Located on the arm and leg · the contributor is 40–49, female · this is a close-up image:
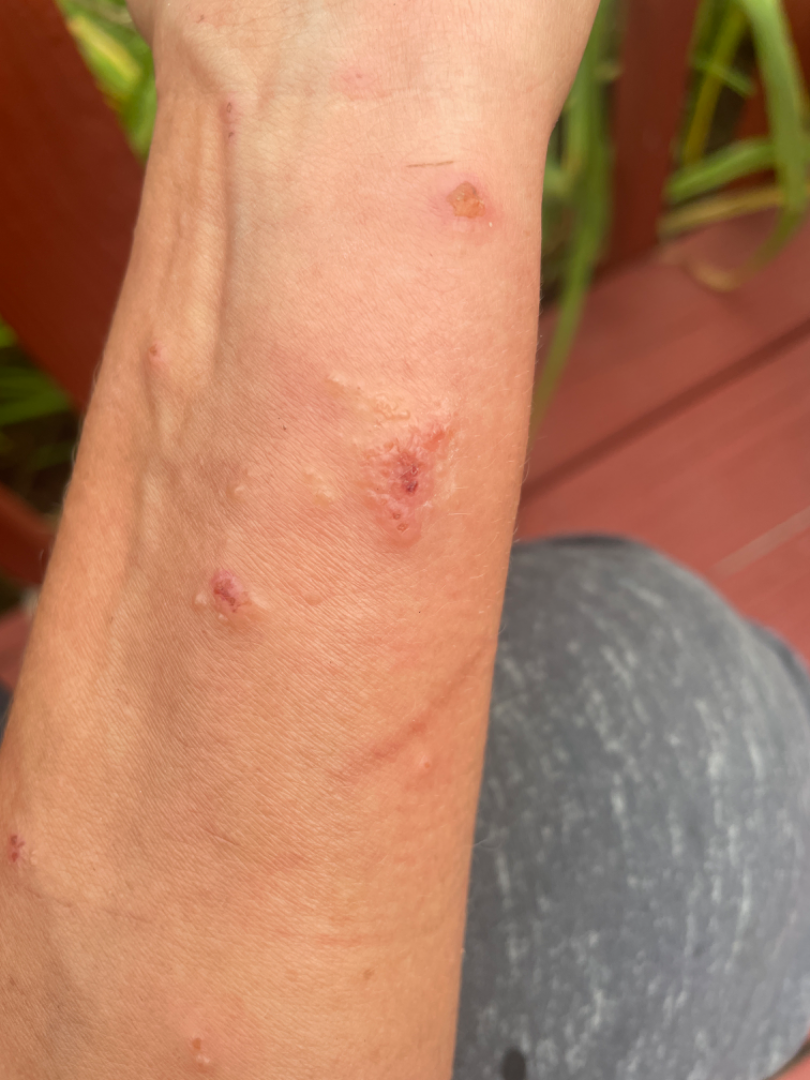On dermatologist assessment of the image: Allergic Contact Dermatitis (0.57); Contact dermatitis (0.29); Herpes Zoster (0.14).